A dermatoscopic image of a skin lesion, a female subject aged 43-47:
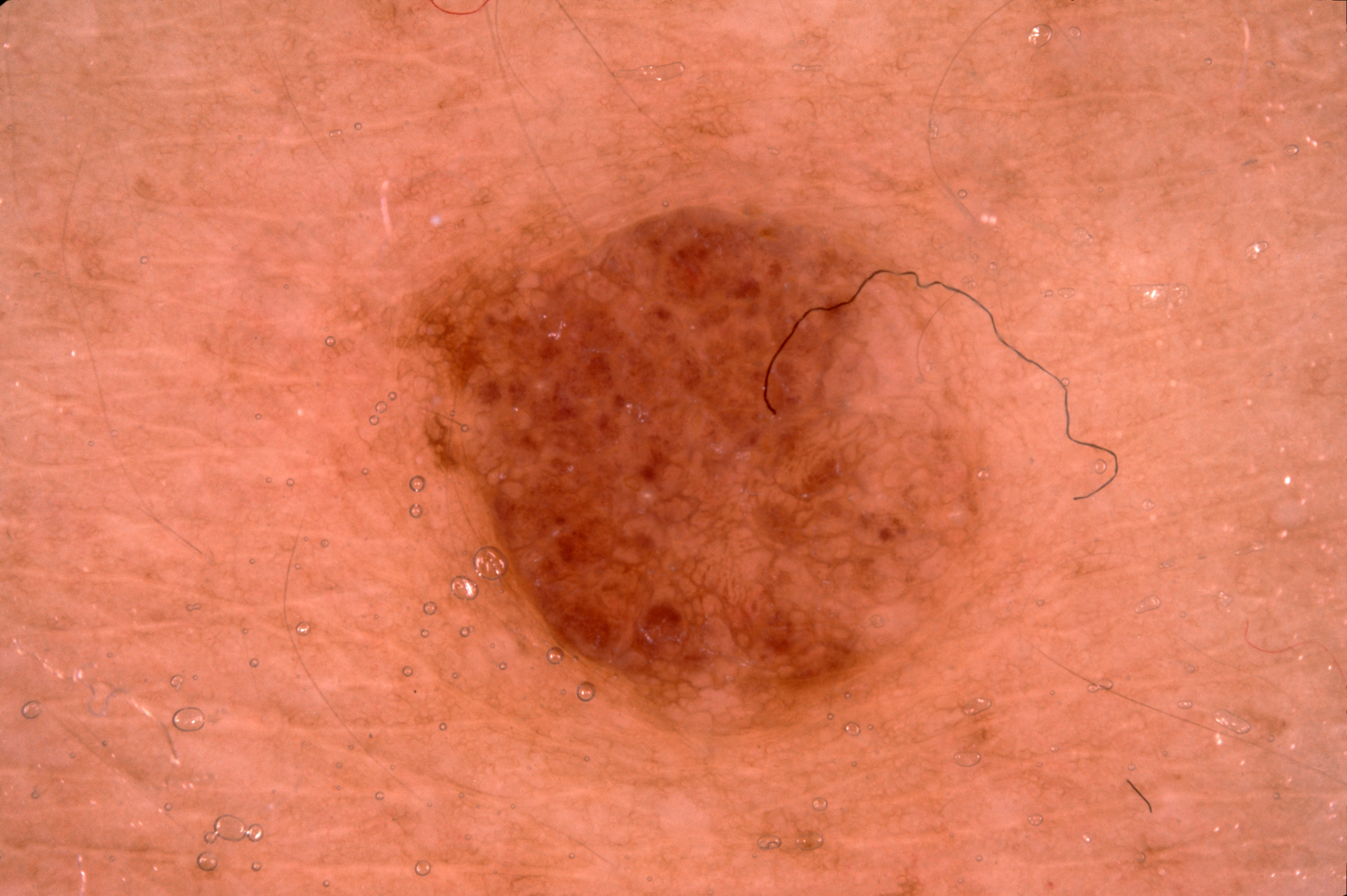The dermoscopic pattern shows milia-like cysts and pigment network, with no negative network or streaks.
The lesion occupies the region [389,203,989,735].
Consistent with a melanocytic nevus, a benign skin lesion.